A dermoscopy image of a single skin lesion:
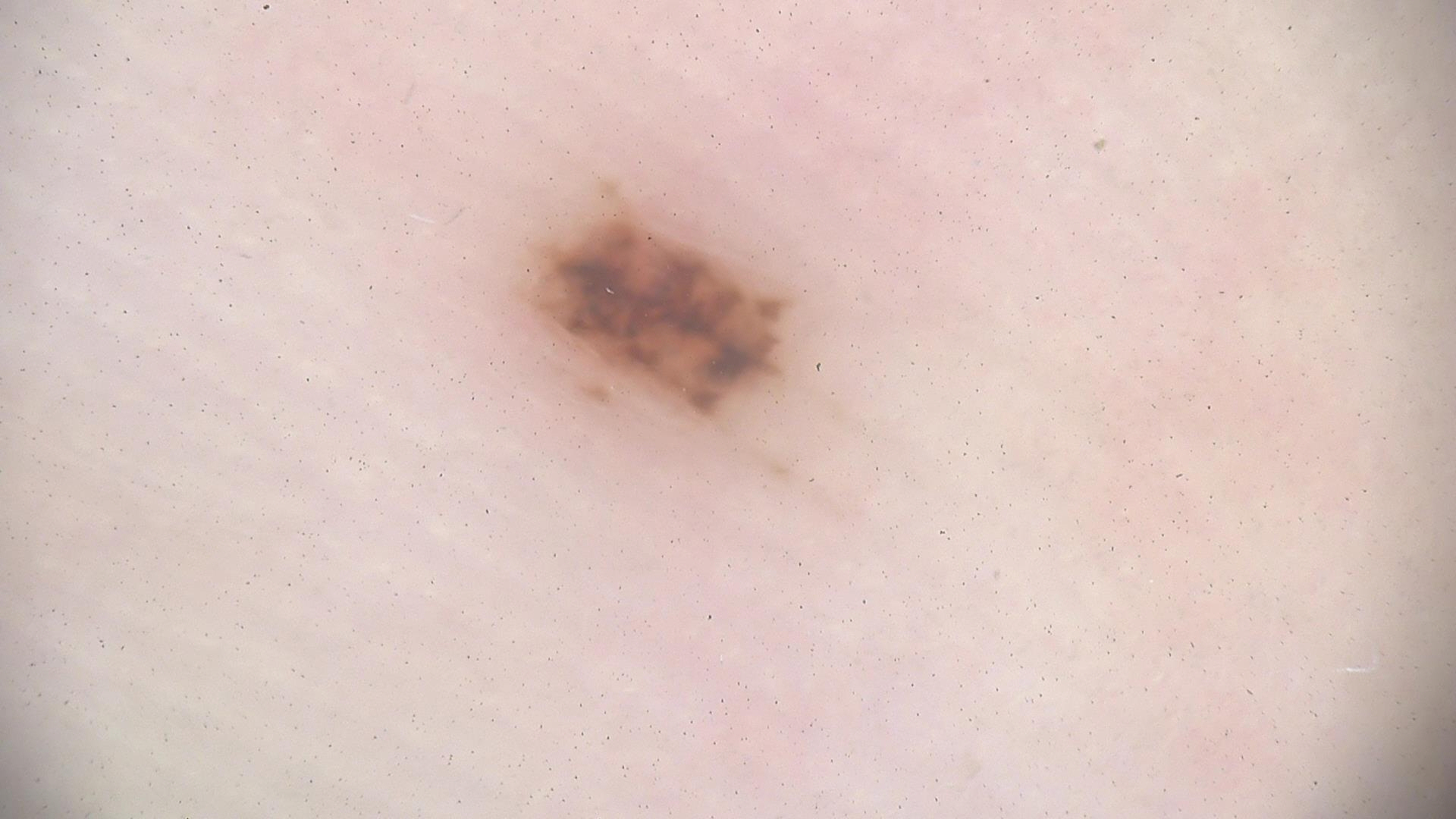Impression: The diagnostic label was a benign lesion — an acral dysplastic junctional nevus.